A female subject 59 years old · by history, pesticide exposure · a smartphone photograph of a skin lesion · FST III:
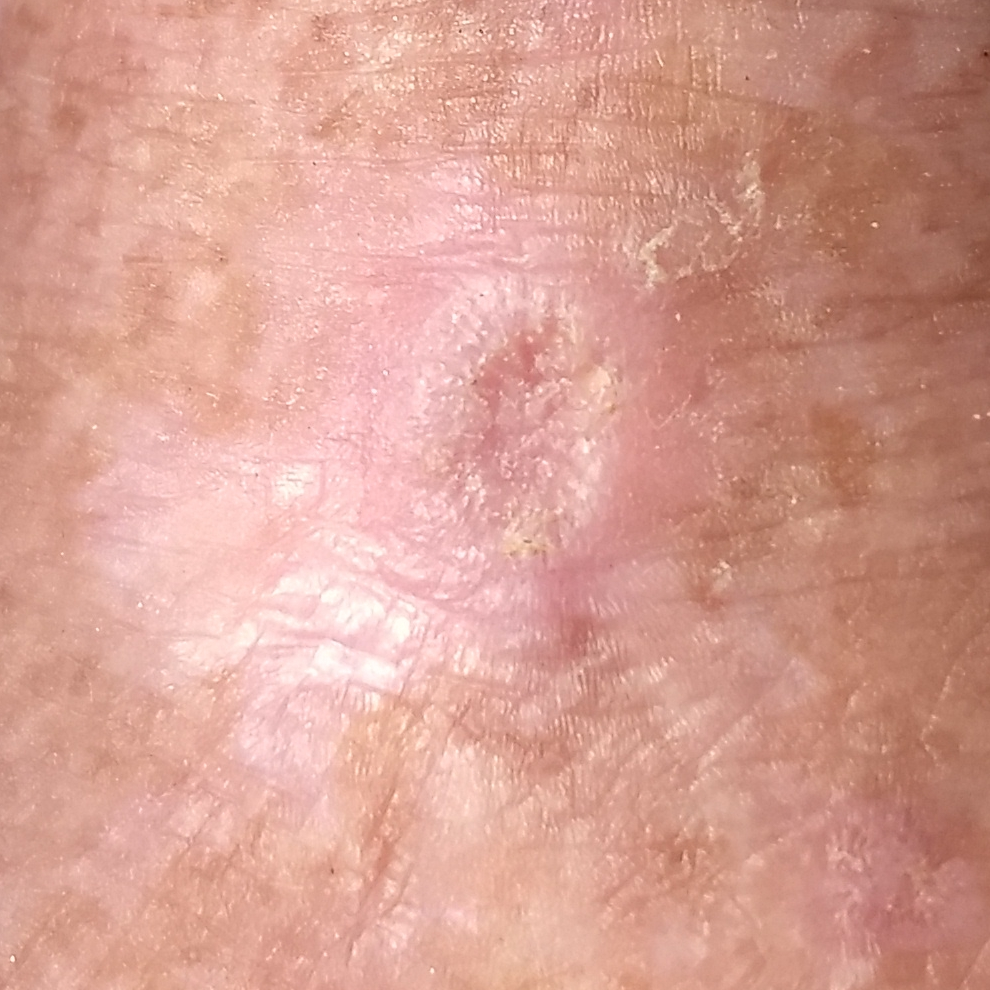The lesion is on a foot.
The patient reports that the lesion is elevated.
Histopathological examination showed an actinic keratosis.